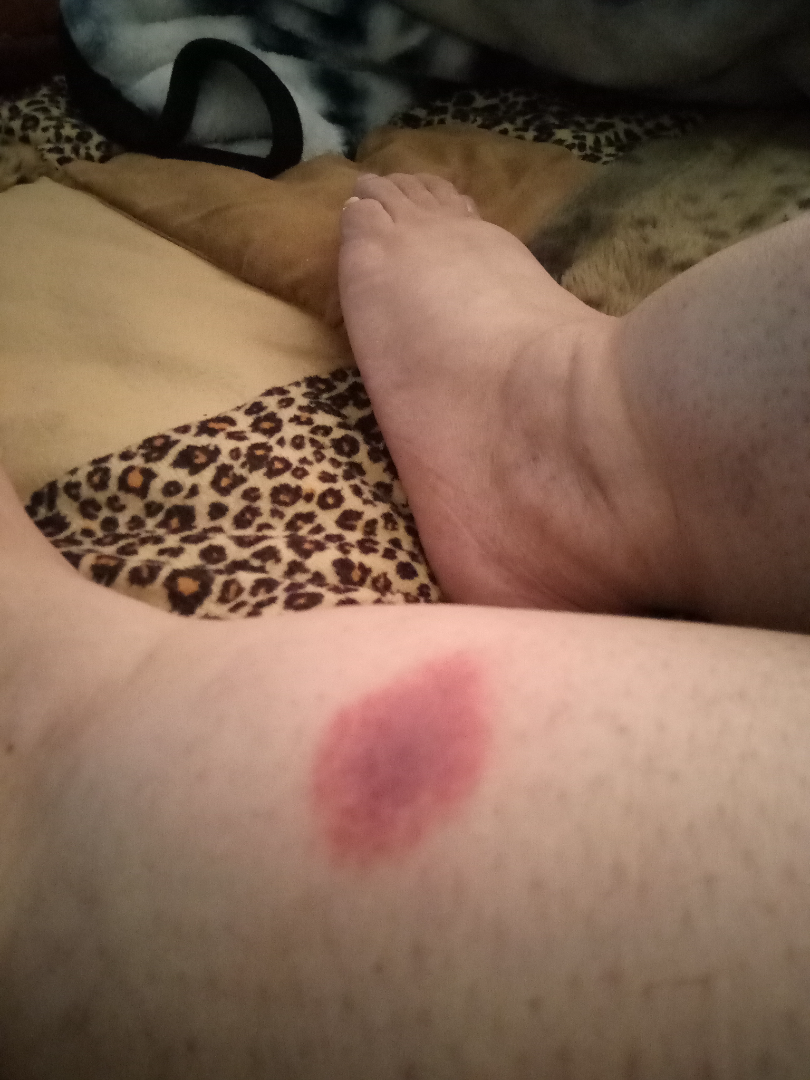constitutional symptoms = none reported | described texture = rough or flaky | photo taken = at an angle | site = leg | diagnostic considerations = most likely Insect Bite.